The head or neck is involved · close-up view — 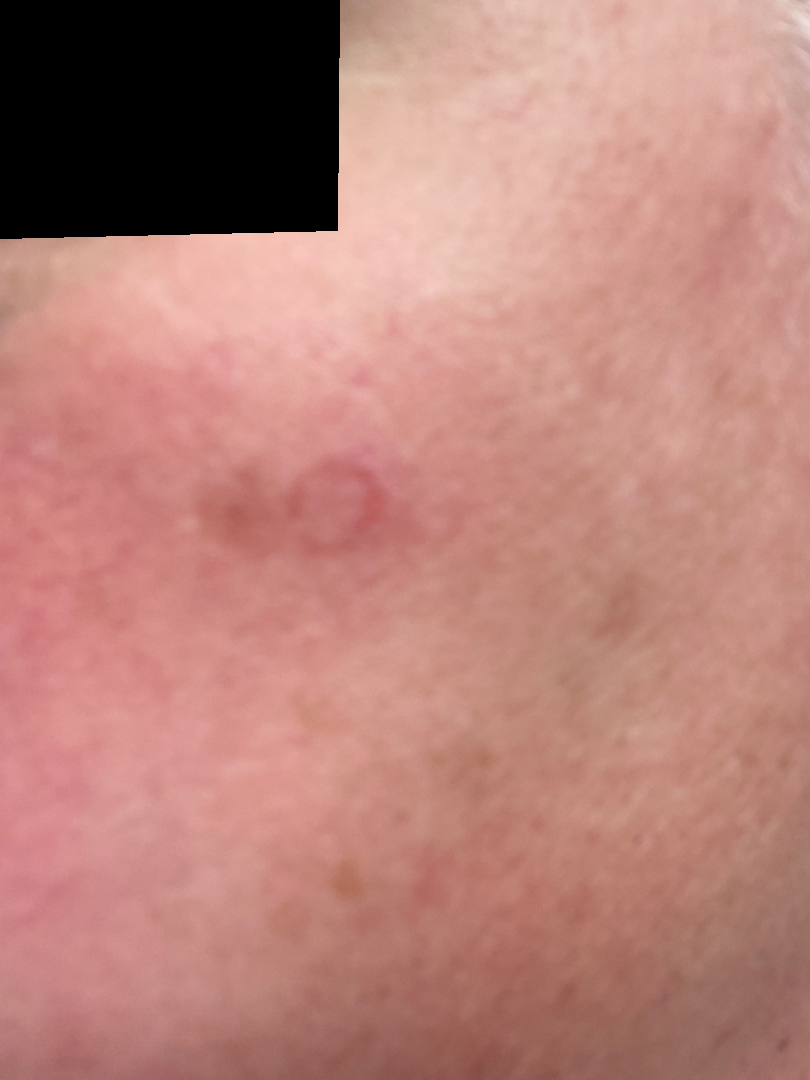No differential diagnosis could be assigned on photographic review.